The subject is 30–39, male. This is a close-up image: 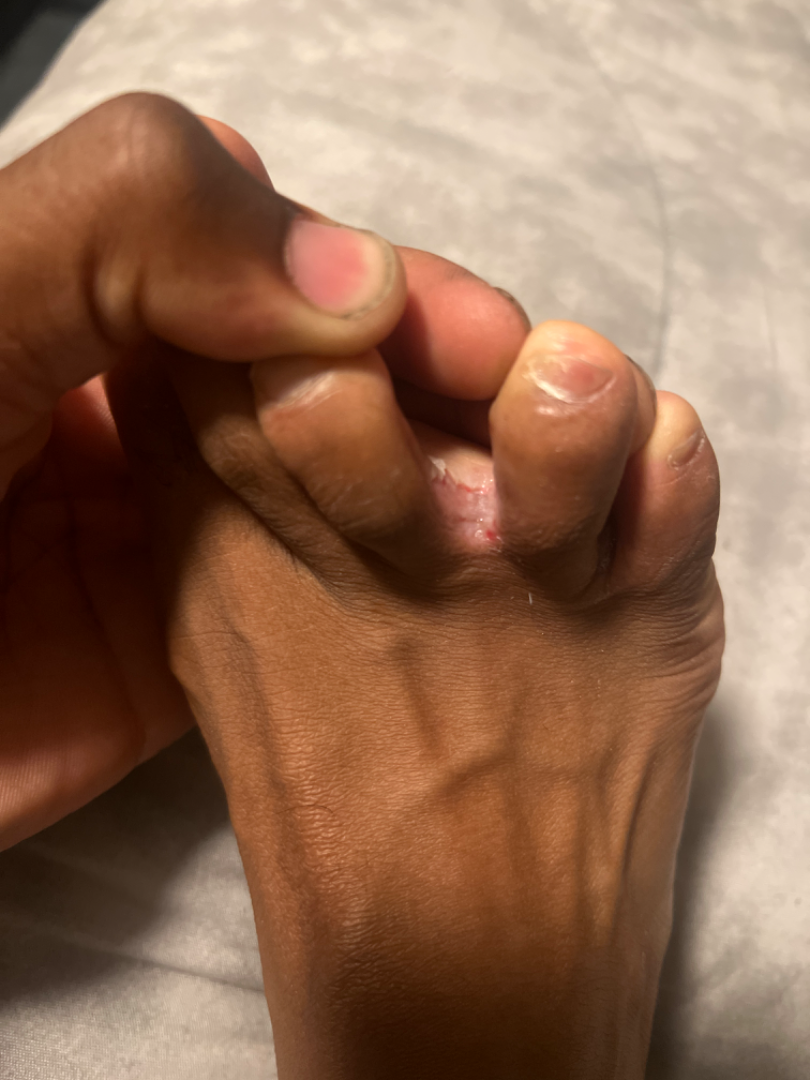Findings: The reviewing clinician's impression was: Tinea (leading); Intertrigo (possible); Infection of toe web (possible).